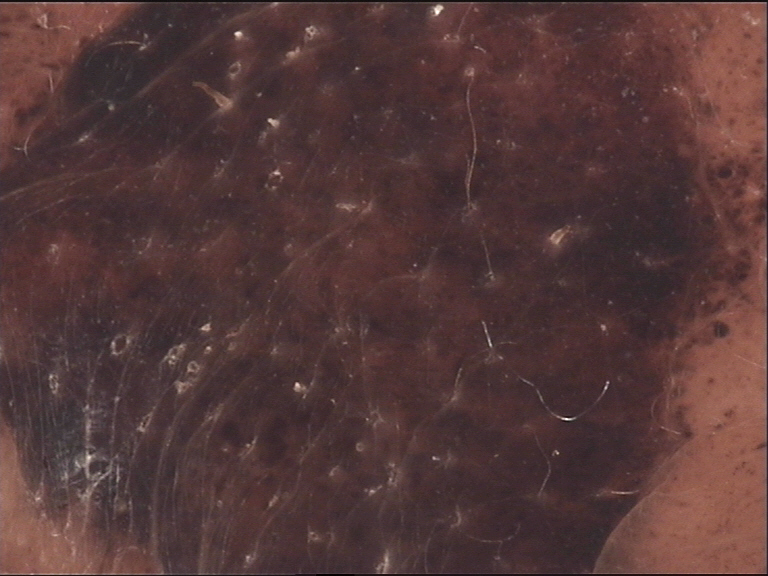image: dermatoscopy
diagnosis:
  name: congenital compound nevus
  code: ccb
  malignancy: benign
  super_class: melanocytic
  confirmation: expert consensus